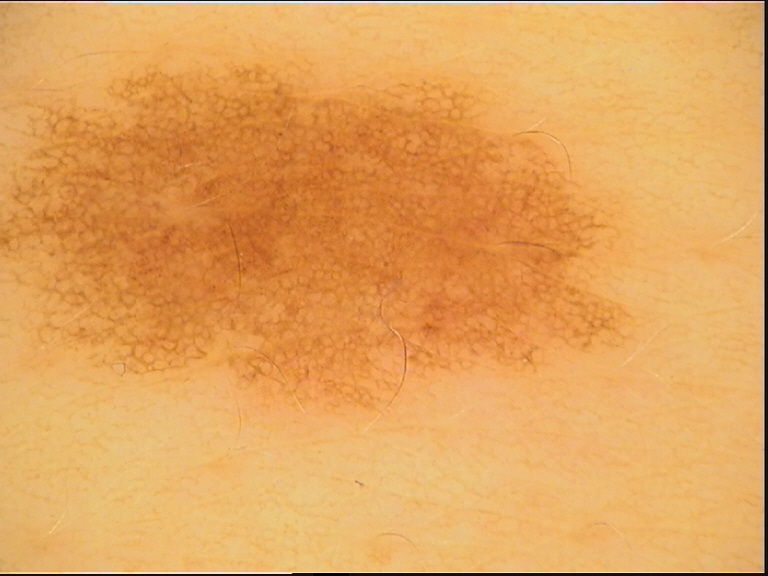This is a banal lesion. The diagnosis was a junctional nevus.